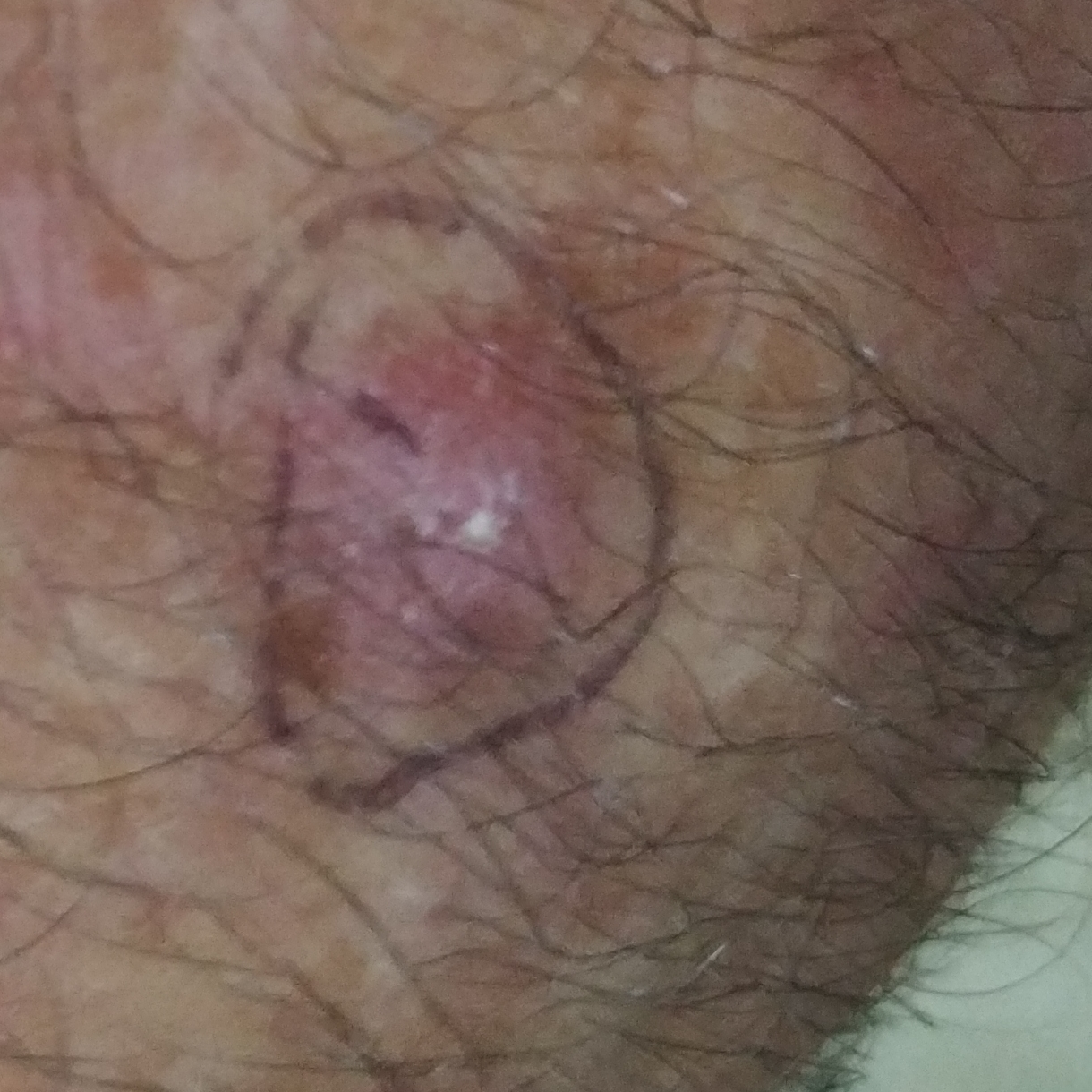skin phototype: I
patient: male, age 69
imaging: clinical photograph
location: the face
lesion size: approx. 5 × 5 mm
symptoms: growth, elevation
diagnosis: basal cell carcinoma (biopsy-proven)